Dermoscopy of a skin lesion:
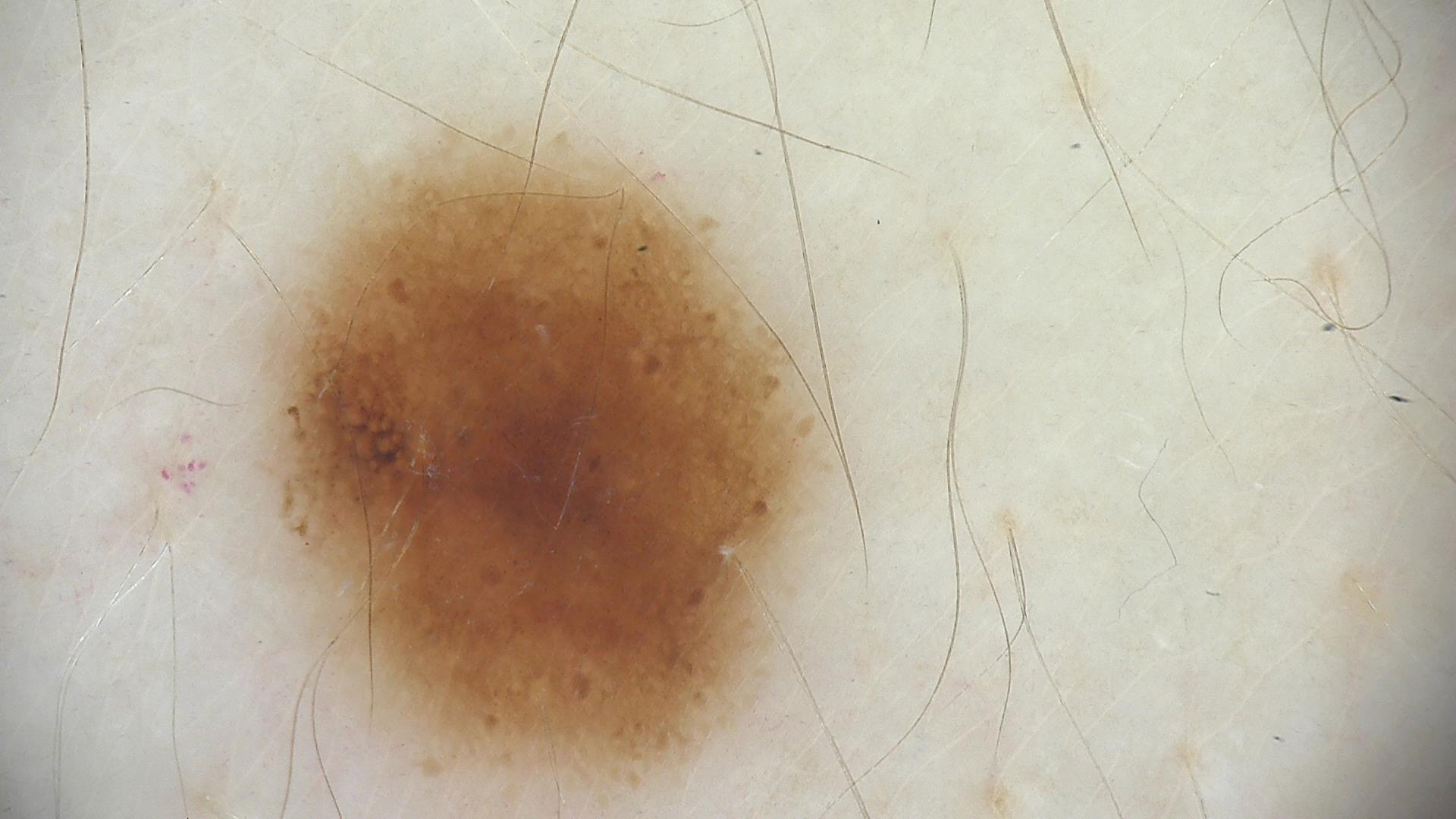Impression: Labeled as a benign lesion — a dysplastic junctional nevus.